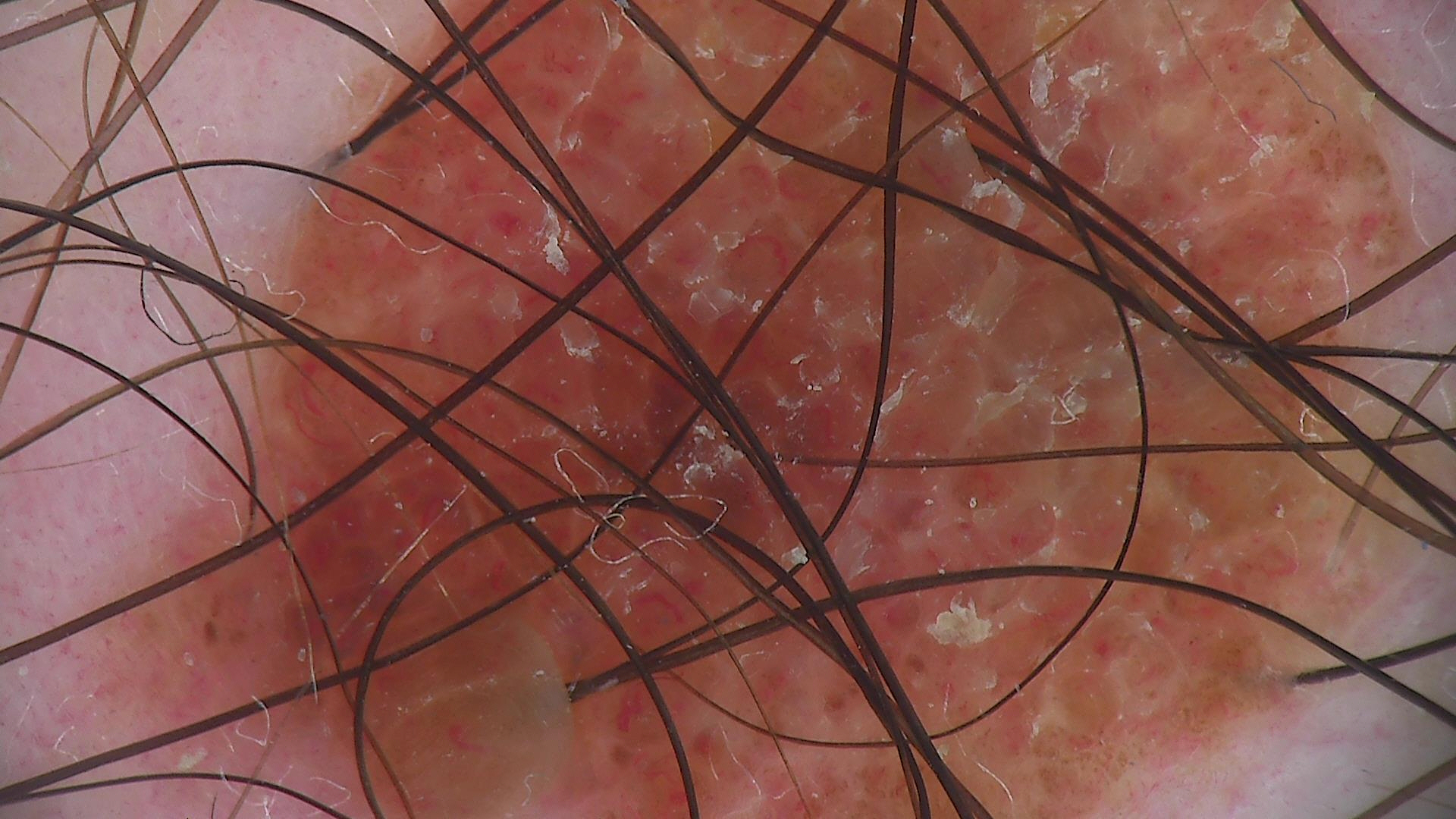Conclusion: Classified as a dermal nevus.